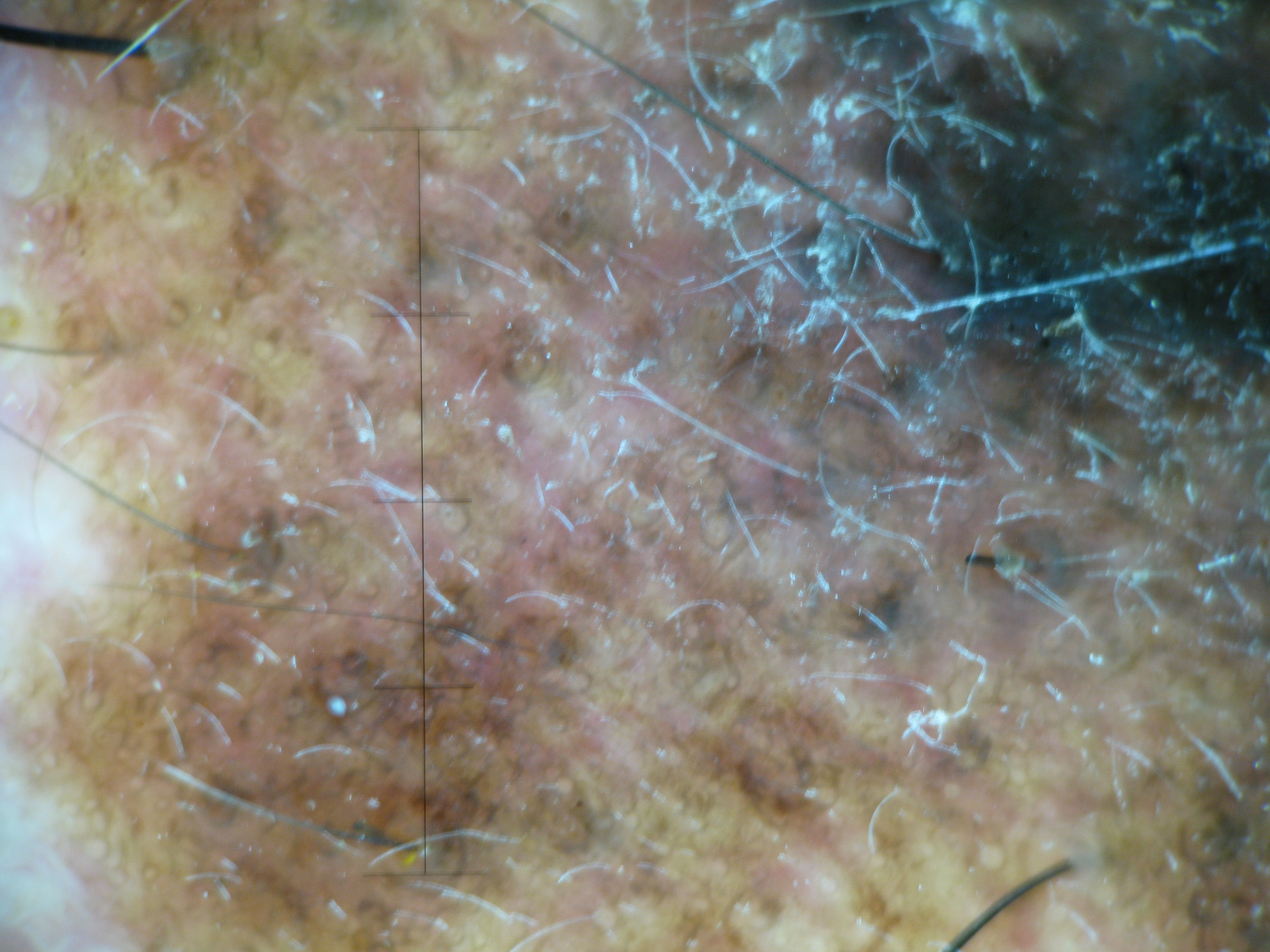<dermoscopy>
  <diagnosis>
    <name>lentigo maligna melanoma</name>
    <code>lmm</code>
    <malignancy>malignant</malignancy>
    <super_class>melanocytic</super_class>
    <confirmation>histopathology</confirmation>
  </diagnosis>
</dermoscopy>